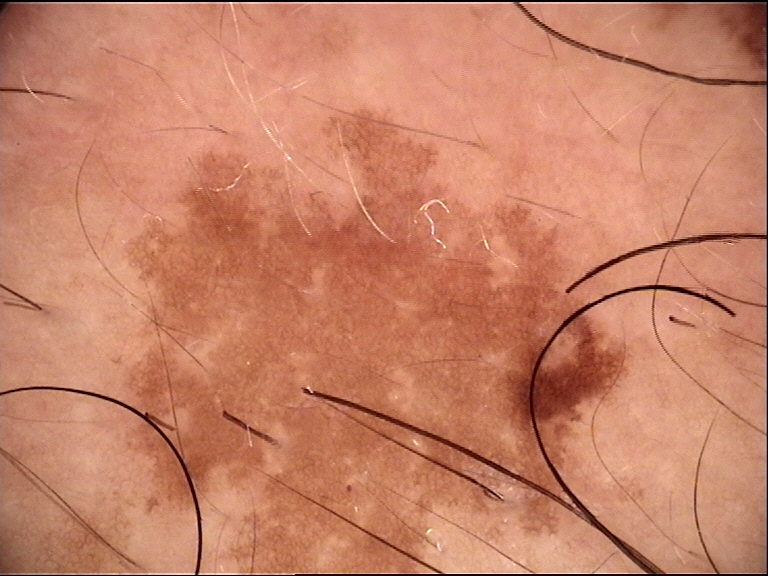Case:
* image — dermatoscopy
* class — dysplastic junctional nevus (expert consensus)